Located on the front of the torso, back of the torso and leg · a close-up photograph.
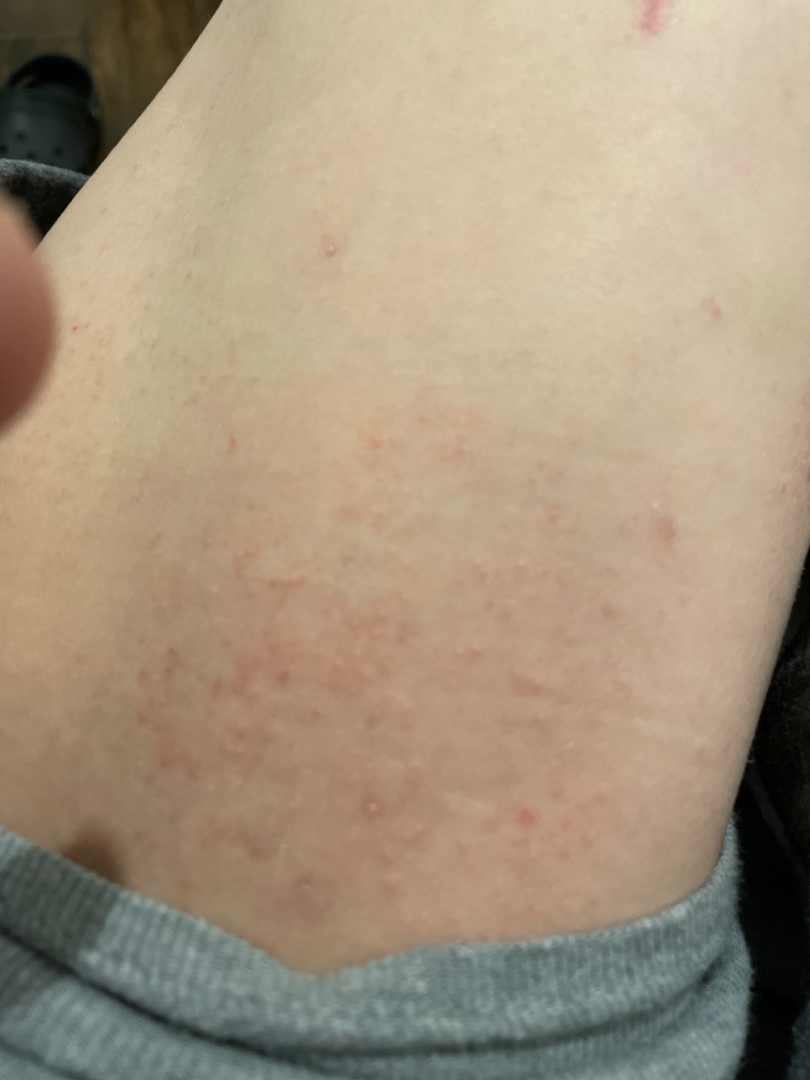assessment = indeterminate from the photograph